The leg is involved, the photograph is a close-up of the affected area: 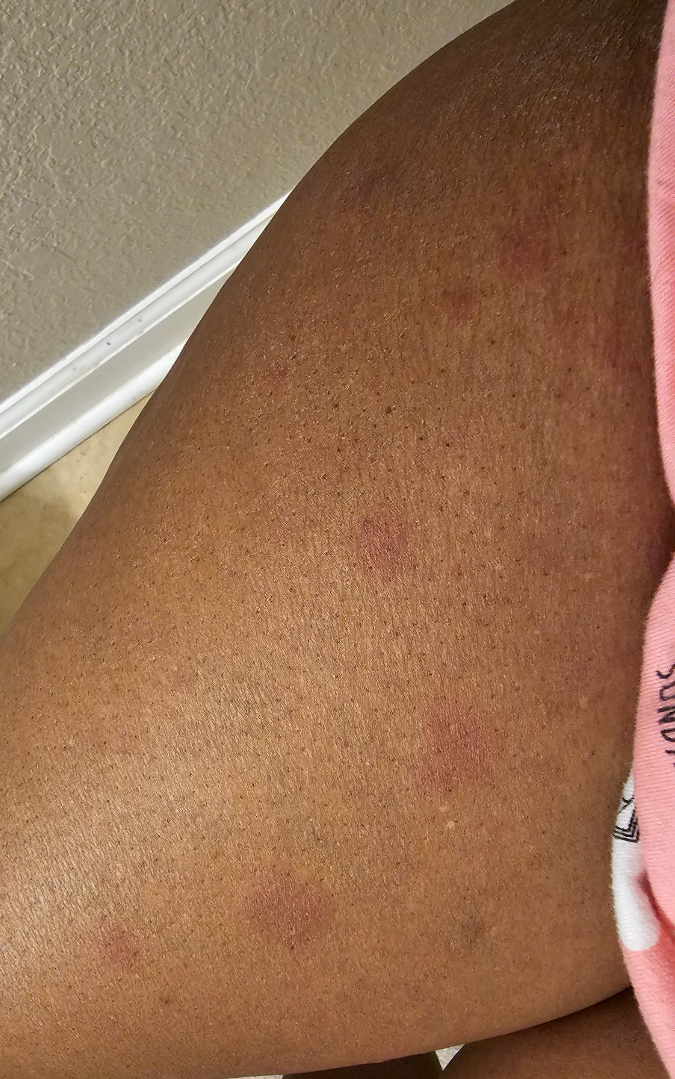assessment=the differential is split between Pityriasis rosea, Cutaneous T Cell Lymphoma and Eczema.